A clinical photograph of a skin lesion · a subject in their late 20s: 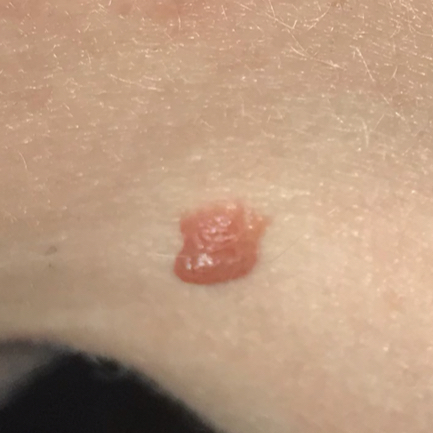| feature | finding |
|---|---|
| anatomic site | the neck |
| patient-reported symptoms | elevation / no growth, no bleeding |
| assessment | nevus (clinical consensus) |